The patient described the issue as a rash; the patient is 30–39, female; symptoms reported: burning, itching and enlargement; close-up view: 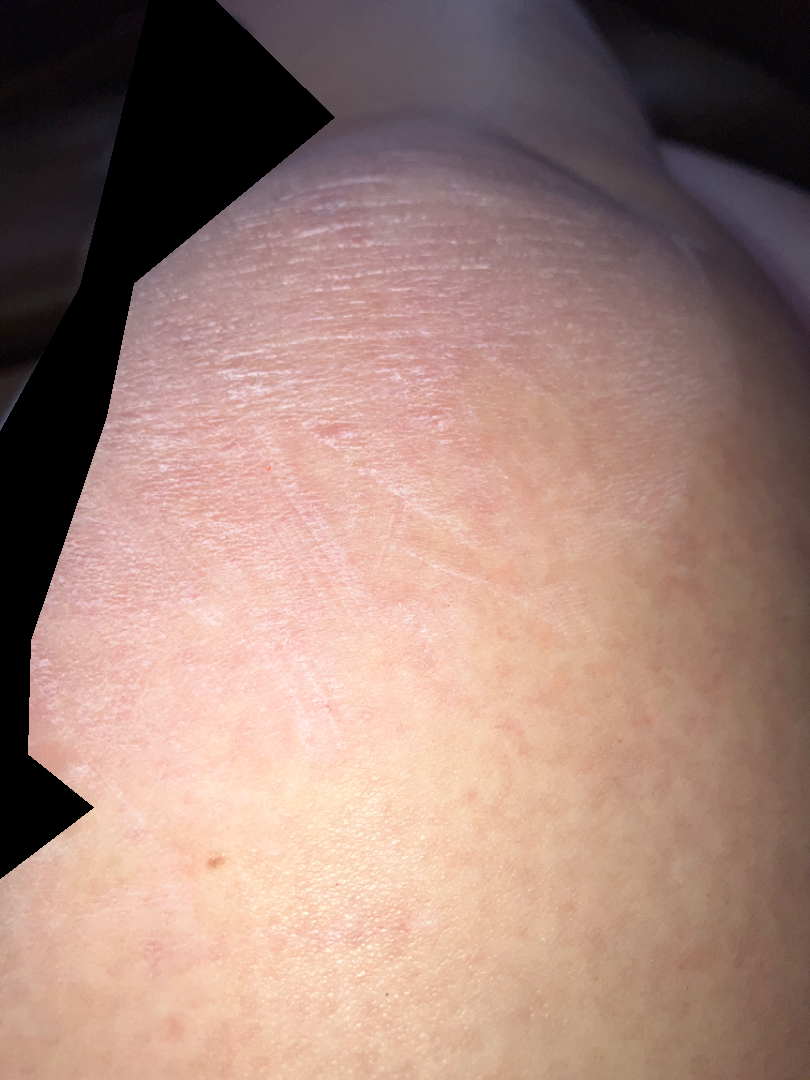{"assessment": "indeterminate from the photograph"}